Located on the arm; this image was taken at an angle: 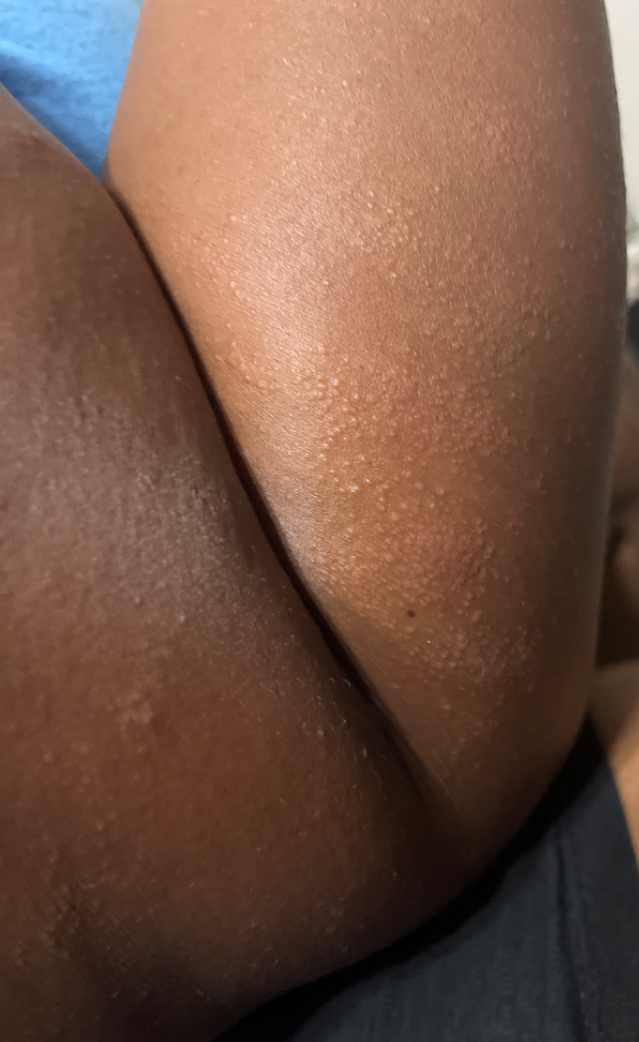On dermatologist assessment of the image, the impression is Miliaria.